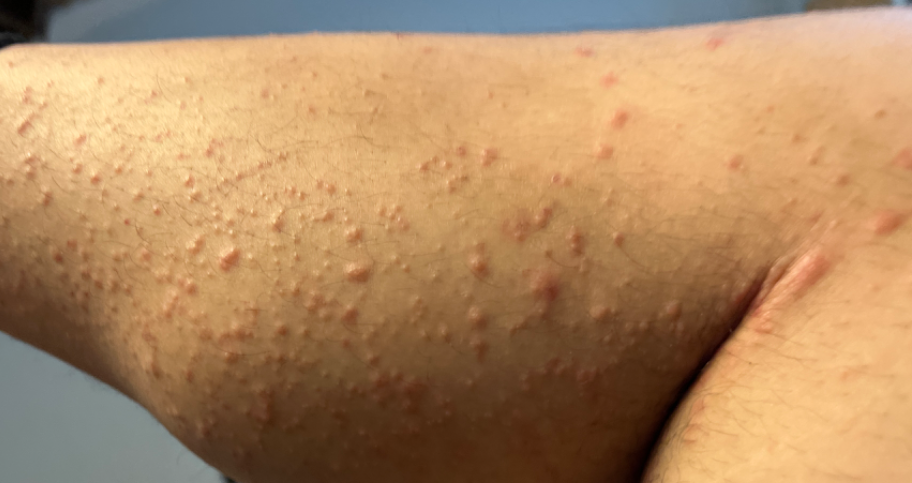{"skin_tone": {"fitzpatrick": "II"}, "body_site": "leg", "patient": "male, age 18–29", "duration": "less than one week", "systemic_symptoms": "none reported", "patient_category": "a rash", "shot_type": "close-up", "texture": "raised or bumpy", "differential": {"tied_lead": ["Folliculitis", "Eczema"], "unlikely": ["Scabies", "Allergic Contact Dermatitis"]}}